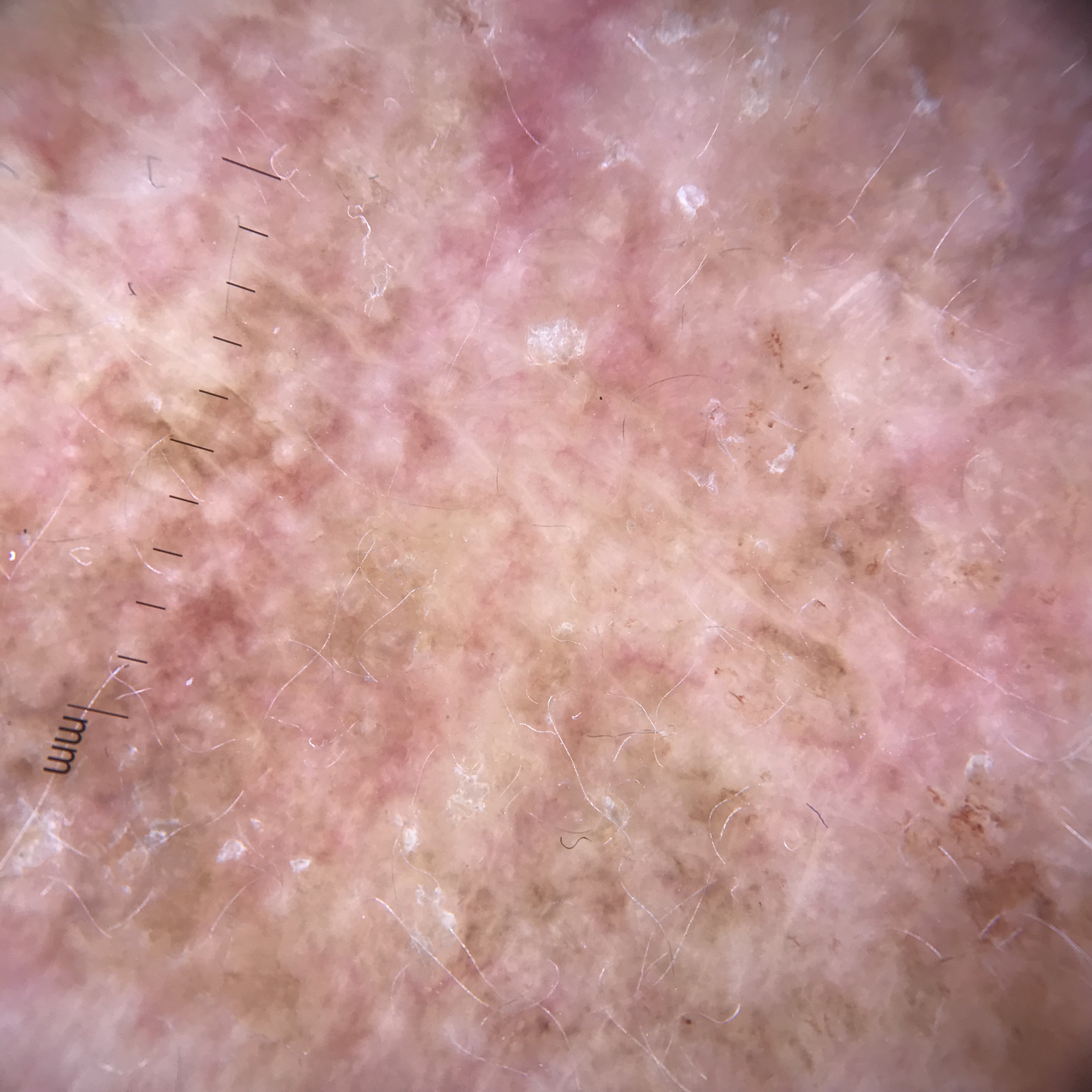A skin lesion imaged with a dermatoscope. This is a keratinocytic lesion. The diagnostic label was an actinic keratosis.